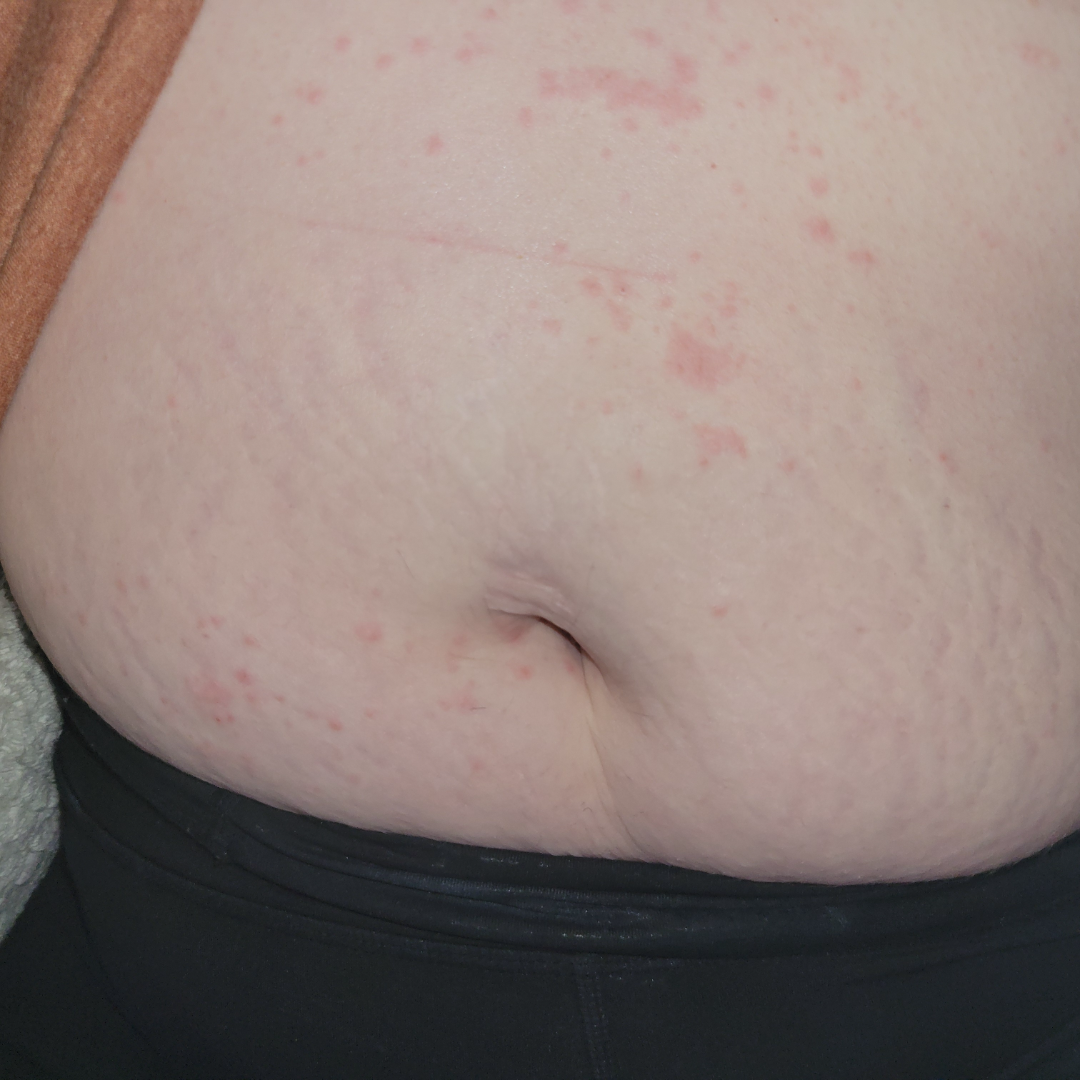{
  "assessment": "indeterminate"
}